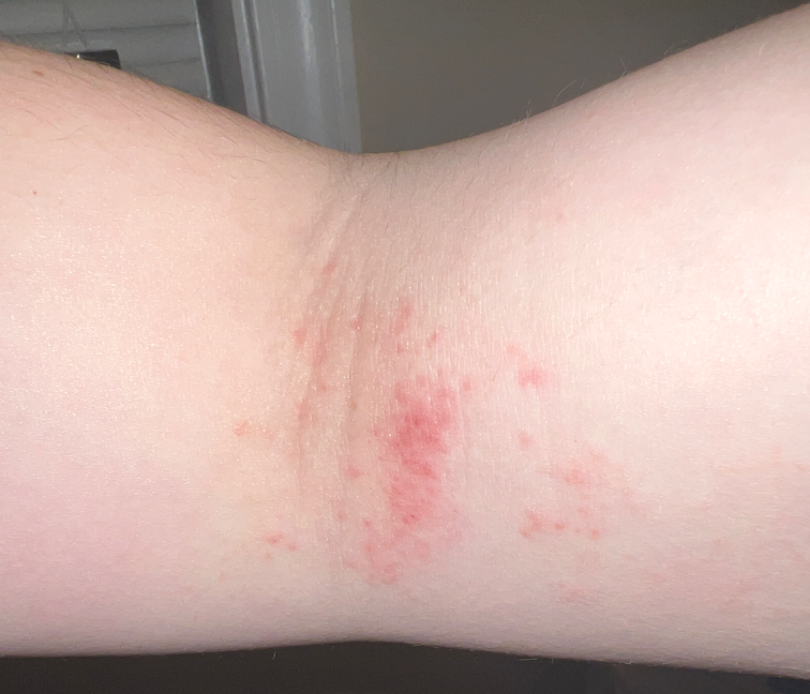The reviewing dermatologist's impression was: consistent with Eczema.